The contributor reports itching; the subject is 60–69, female; texture is reported as fluid-filled; this is a close-up image; no associated systemic symptoms reported; Fitzpatrick IV — 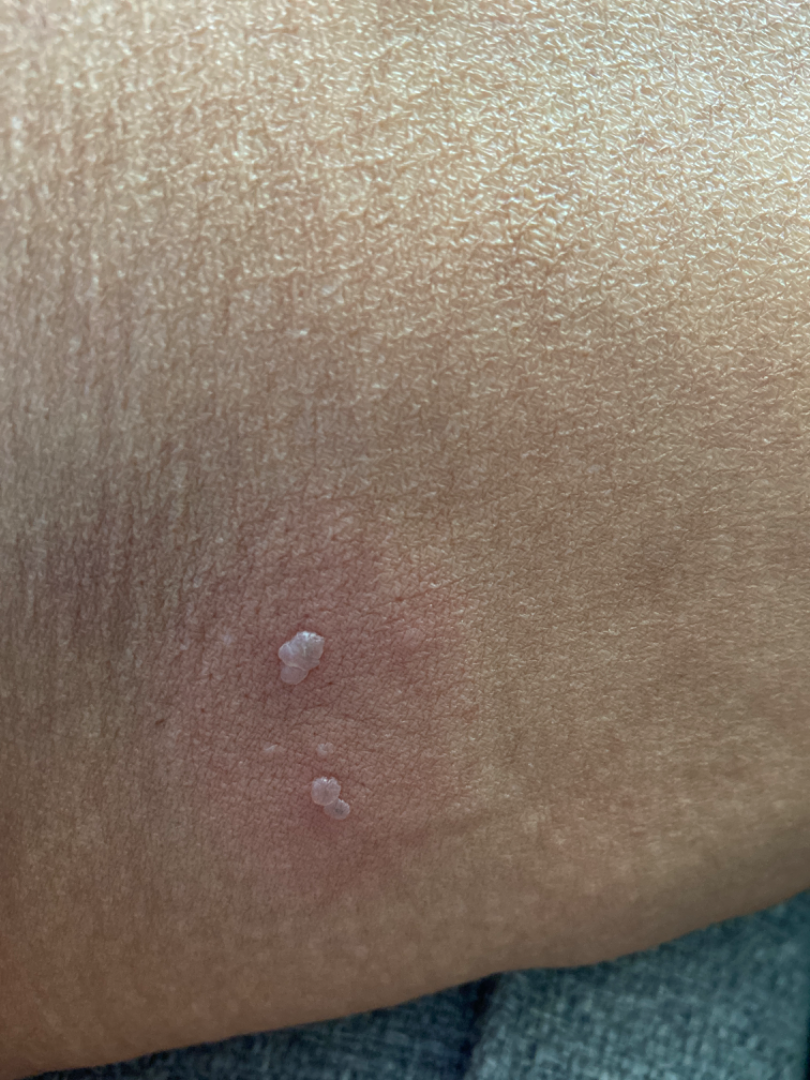Review: Most consistent with Herpes Simplex; possibly Impetigo; with consideration of Herpes Zoster.